A dermoscopic photograph of a skin lesion.
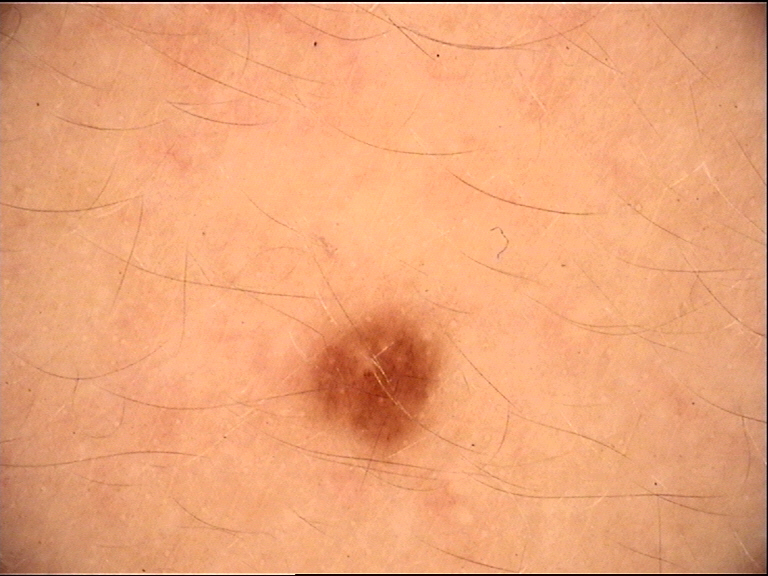Impression:
The diagnostic label was a benign lesion — a dysplastic junctional nevus.